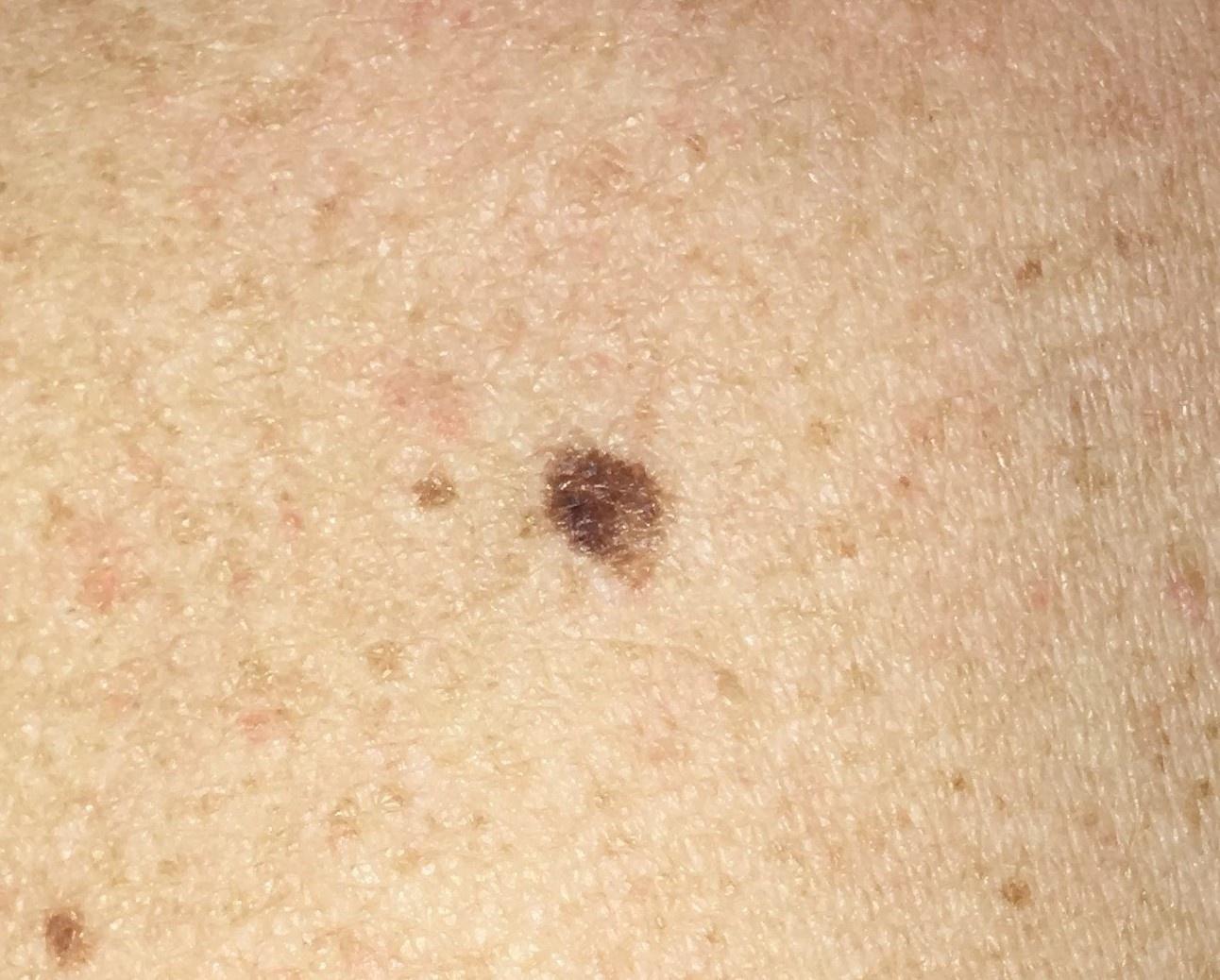Conclusion: On biopsy, the diagnosis was a nevus.